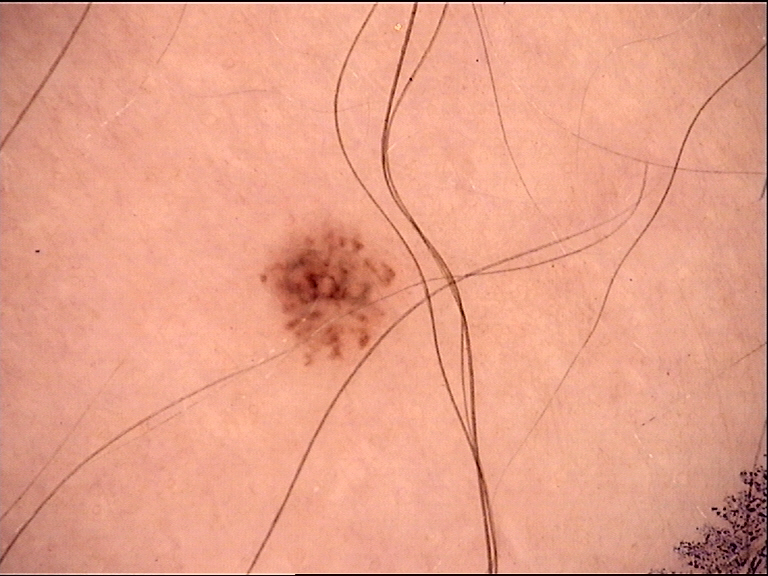The morphology is that of a banal lesion. Diagnosed as a junctional nevus.